The patient is a female aged 30–39 · present for less than one week · the photo was captured at an angle · the lesion is described as raised or bumpy · the arm and back of the hand are involved · FST II:
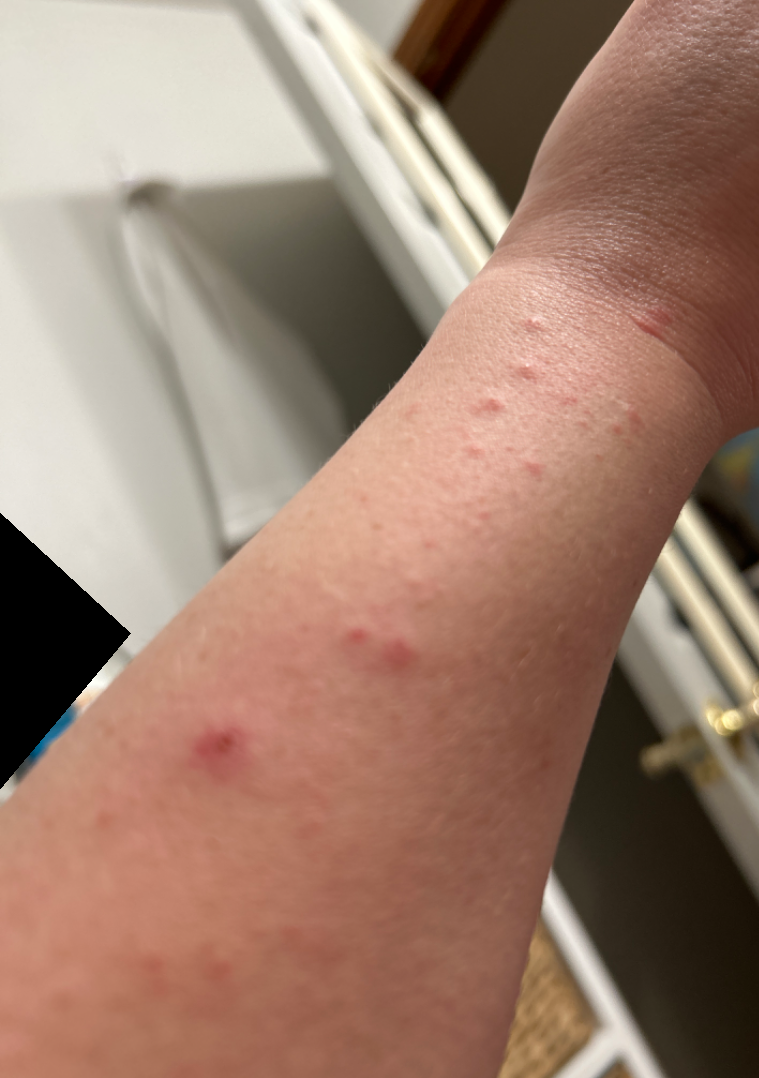| key | value |
|---|---|
| clinical impression | most consistent with Allergic Contact Dermatitis; the differential also includes Urticaria; an alternative is Insect Bite; less likely is Viral Exanthem; less probable is Folliculitis |